A dermoscopic photograph of a skin lesion: 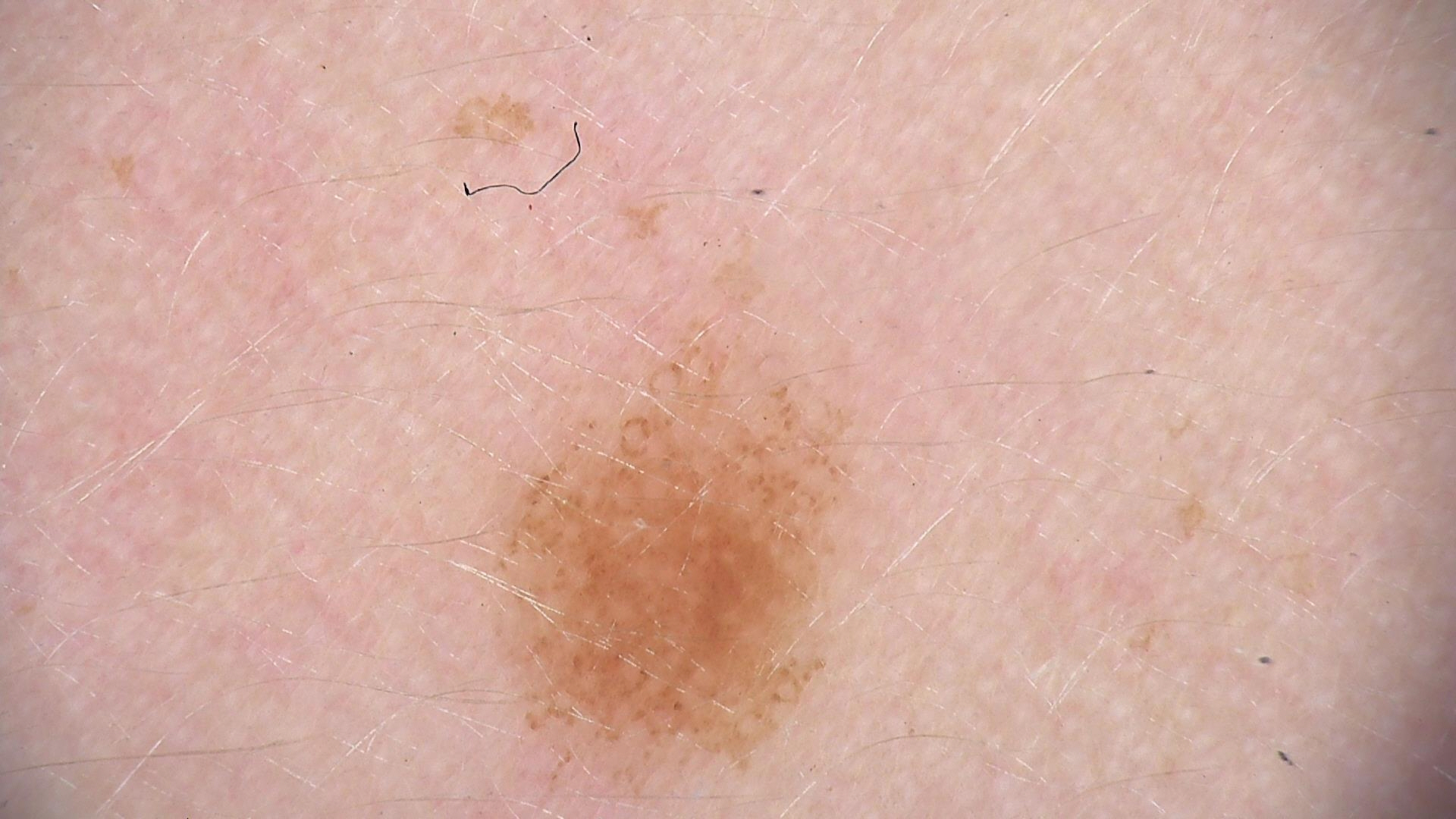<lesion>
<diagnosis>
<name>dysplastic junctional nevus</name>
<code>jd</code>
<malignancy>benign</malignancy>
<super_class>melanocytic</super_class>
<confirmation>expert consensus</confirmation>
</diagnosis>
</lesion>